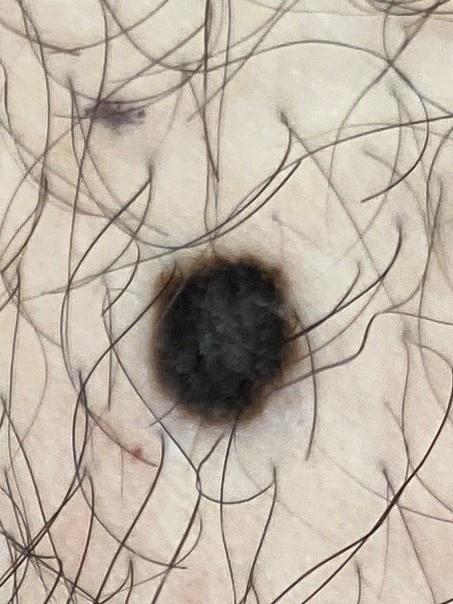A macroscopic clinical photograph of a skin lesion. Confirmed on histopathology as a melanoma.